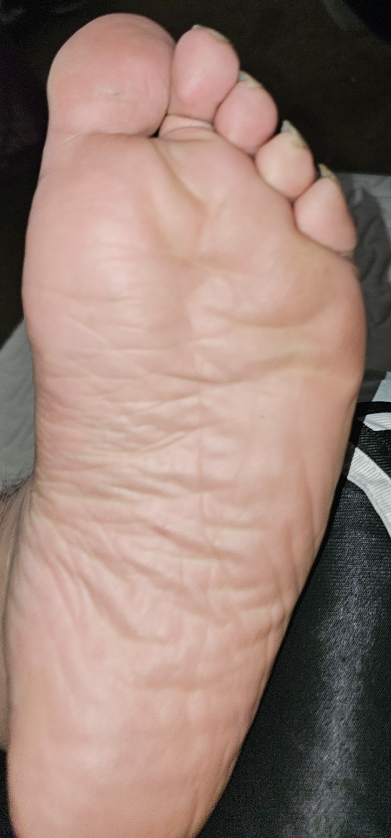The reviewing dermatologist did not identify a discernible skin condition. An image taken at a distance.